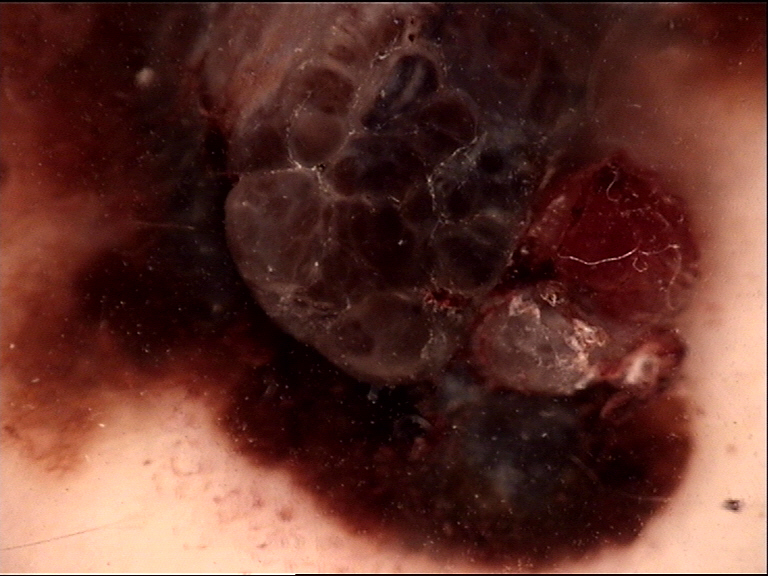<lesion>
<diagnosis>
<name>melanoma</name>
<code>mel</code>
<malignancy>malignant</malignancy>
<super_class>melanocytic</super_class>
<confirmation>histopathology</confirmation>
</diagnosis>
</lesion>